Reported lesion symptoms include pain, burning, itching, enlargement and bothersome appearance. This image was taken at an angle. The patient considered this a rash. Reported duration is less than one week. The lesion is described as raised or bumpy and fluid-filled. The lesion involves the back of the torso and front of the torso.
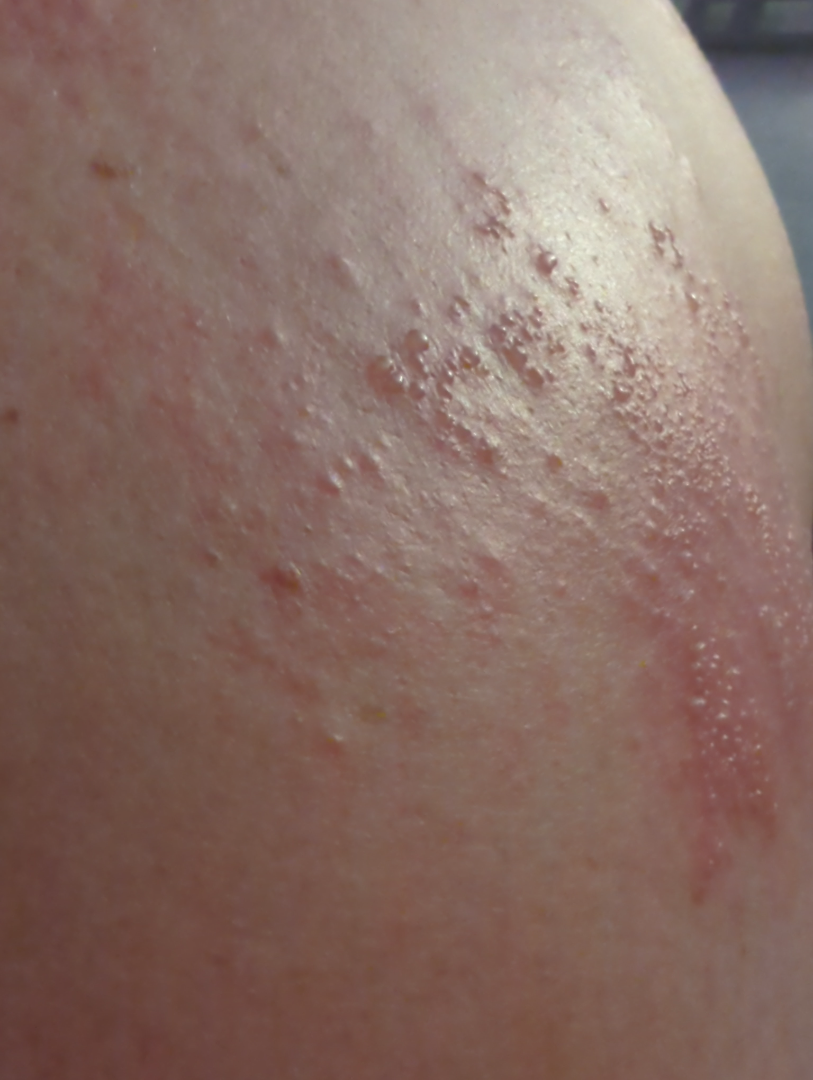Q: What is the dermatologist's impression?
A: Herpes Zoster (possible); Allergic Contact Dermatitis (possible)